The lesion is described as raised or bumpy. Symptoms reported: itching. This image was taken at an angle. The patient indicates the condition has been present for less than one week. Female patient, age 30–39. Located on the leg, front of the torso and arm:
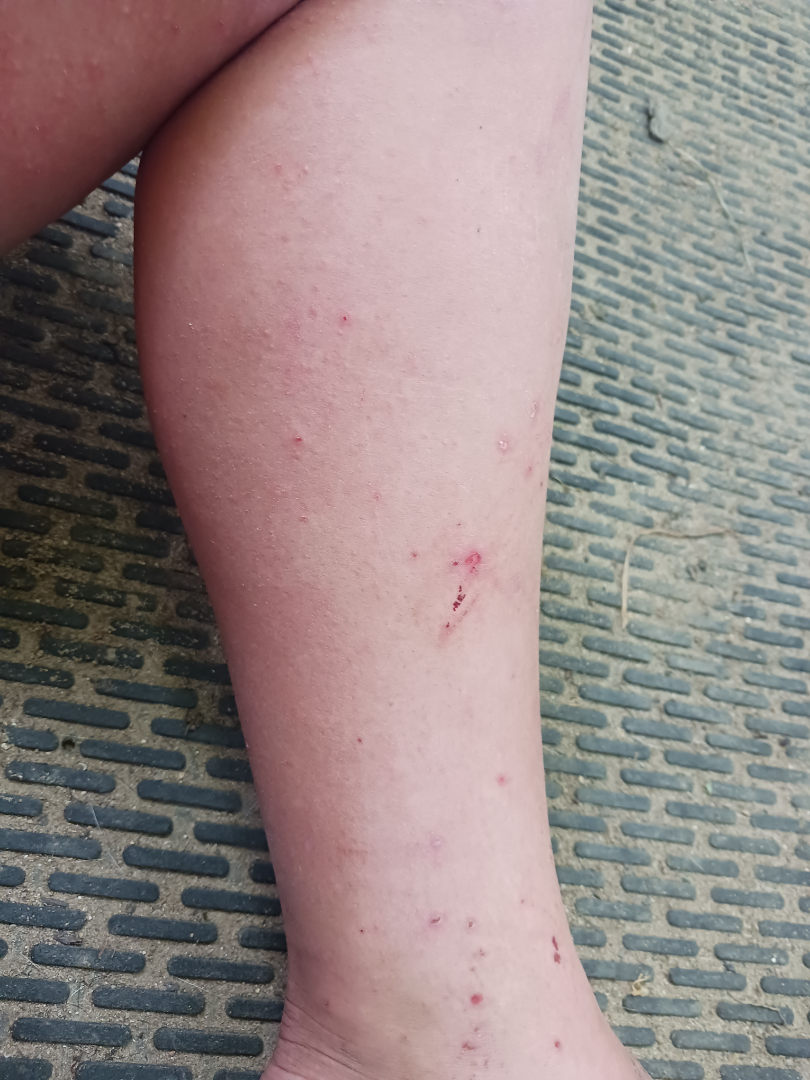| feature | finding |
|---|---|
| differential | in keeping with Acute and chronic dermatitis |